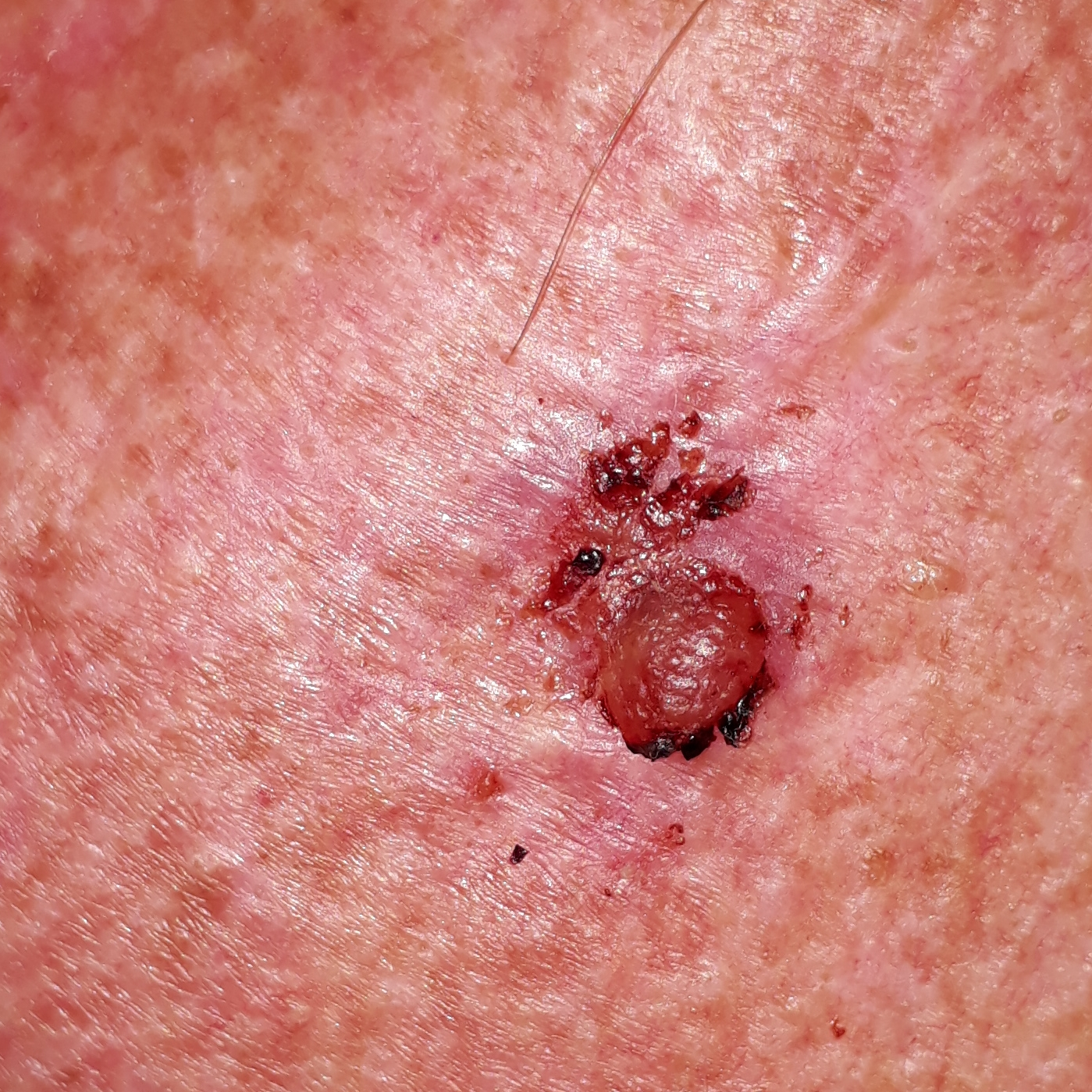A clinical photograph of a skin lesion. The patient was assessed as Fitzpatrick skin type I. Measuring about 13 × 8 mm. By the patient's account, the lesion hurts, has bled, itches, and is elevated. Biopsy-confirmed as a malignant lesion — a basal cell carcinoma.